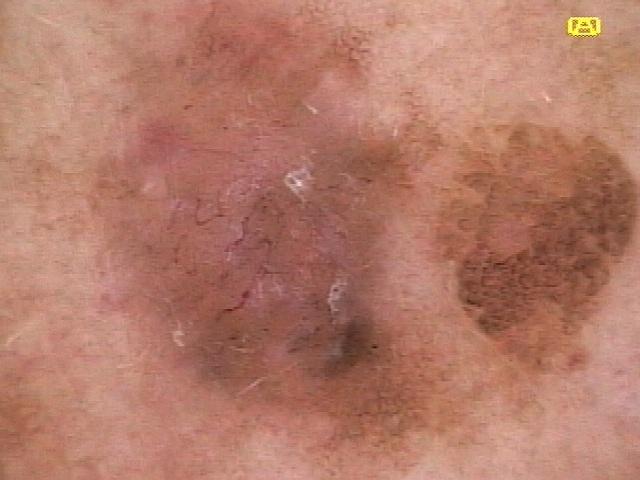{
  "patient": {
    "age_approx": 70,
    "sex": "female"
  },
  "image": "dermoscopic image",
  "diagnosis": {
    "name": "Basal cell carcinoma",
    "malignancy": "malignant",
    "confirmation": "histopathology",
    "lineage": "adnexal"
  }
}